Present for less than one week · the contributor is female · the photograph is a close-up of the affected area · self-categorized by the patient as a rash · the lesion involves the front of the torso, back of the torso, arm and leg · the lesion is described as raised or bumpy · reported lesion symptoms include burning, bothersome appearance and itching · the patient notes associated joint pain — 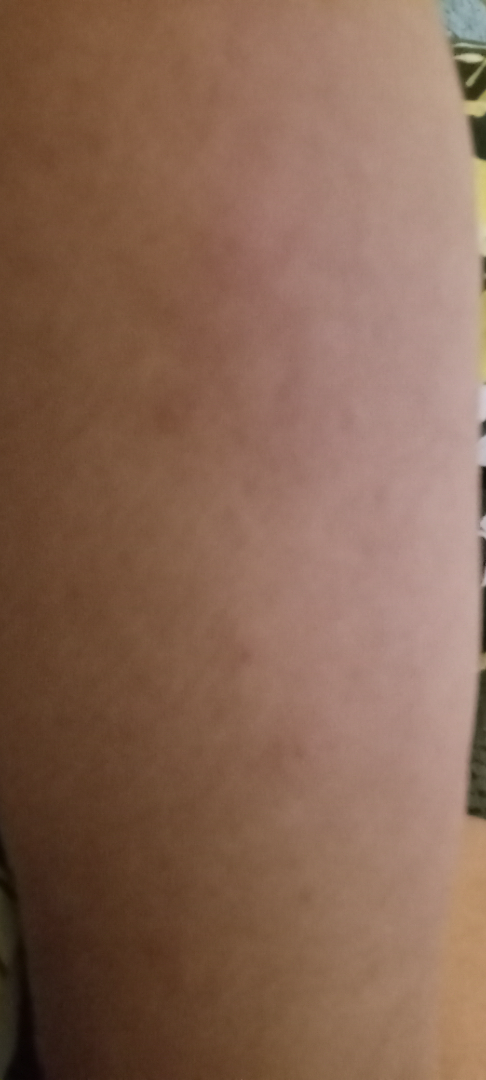assessment: unable to determine